The photo was captured at a distance.
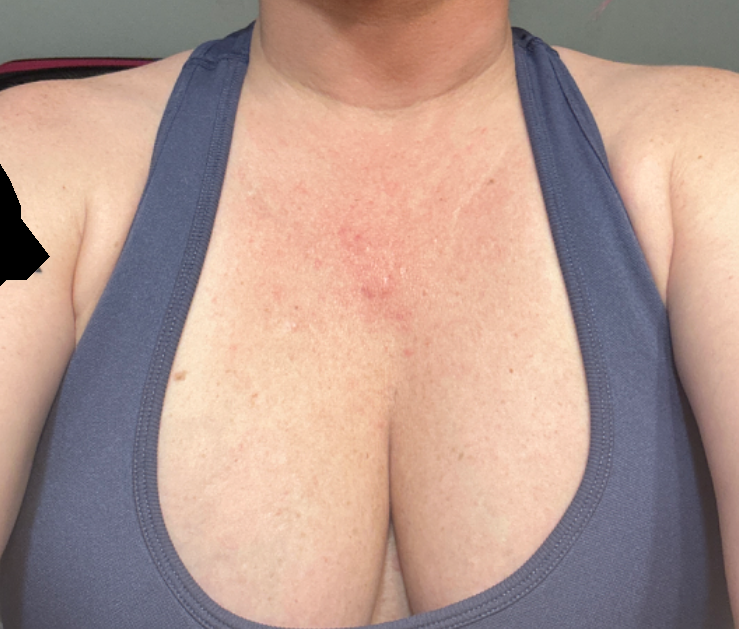assessment = not assessable.